The photograph was taken at a distance; the leg is involved.
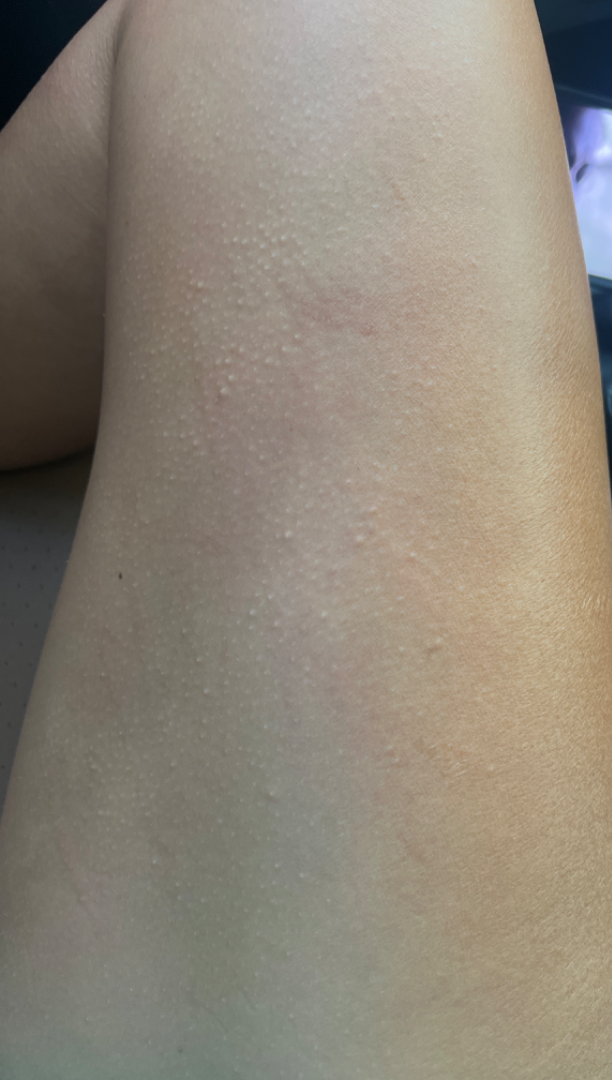other reported symptoms: none reported, self-categorized as: a rash, patient-reported symptoms: itching, symptom duration: one to three months, clinical impression: the leading consideration is Keratosis pilaris; also consider Lichen nitidus; possibly Lichen spinulosus.